A male patient aged 13-17. A dermatoscopic image of a skin lesion.
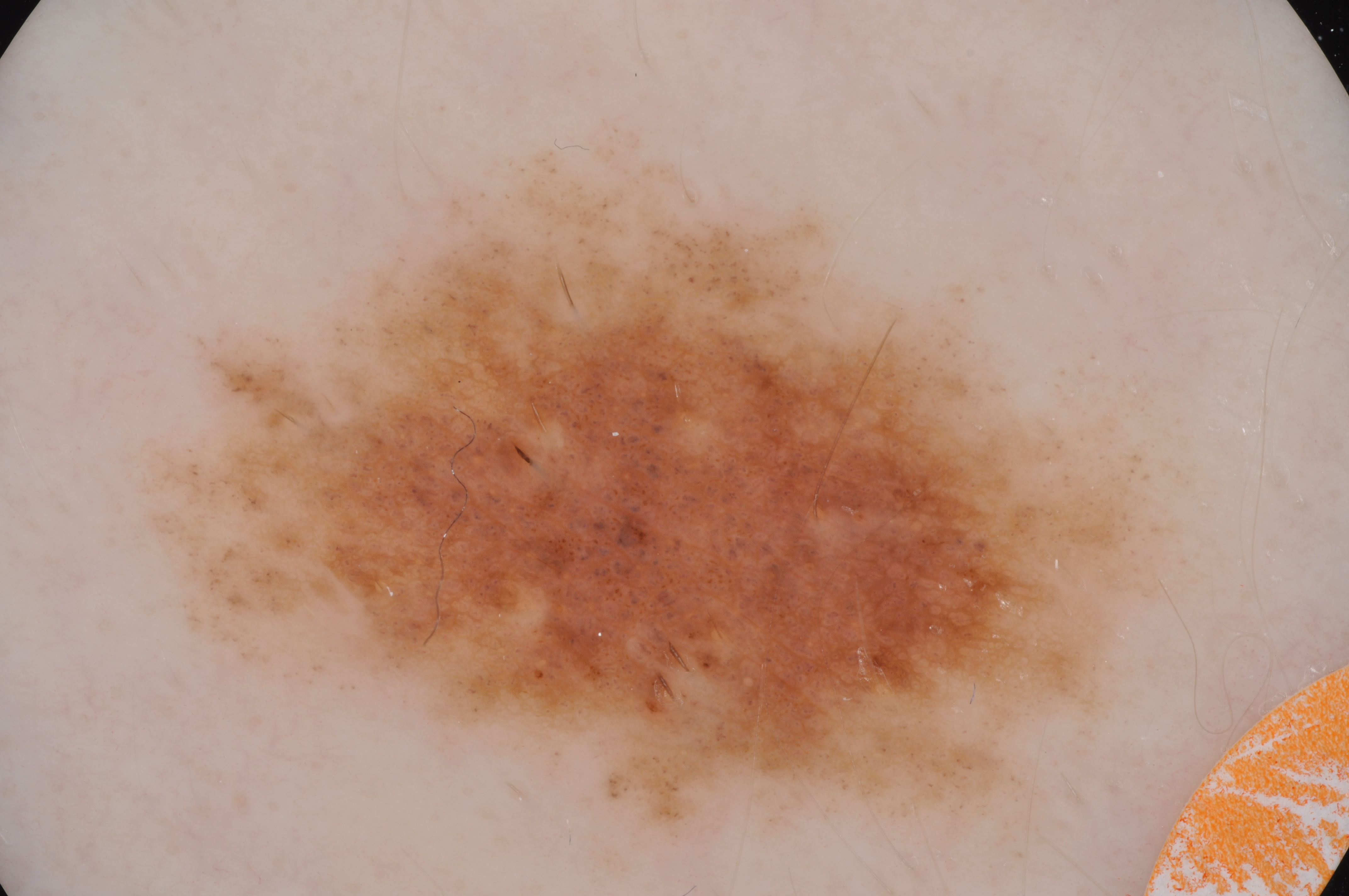Findings:
* dermoscopic features — globules and pigment network; absent: milia-like cysts, streaks, and negative network
* lesion size — large
* location — [151,150,1176,841]
* impression — a melanocytic nevus, a benign lesion